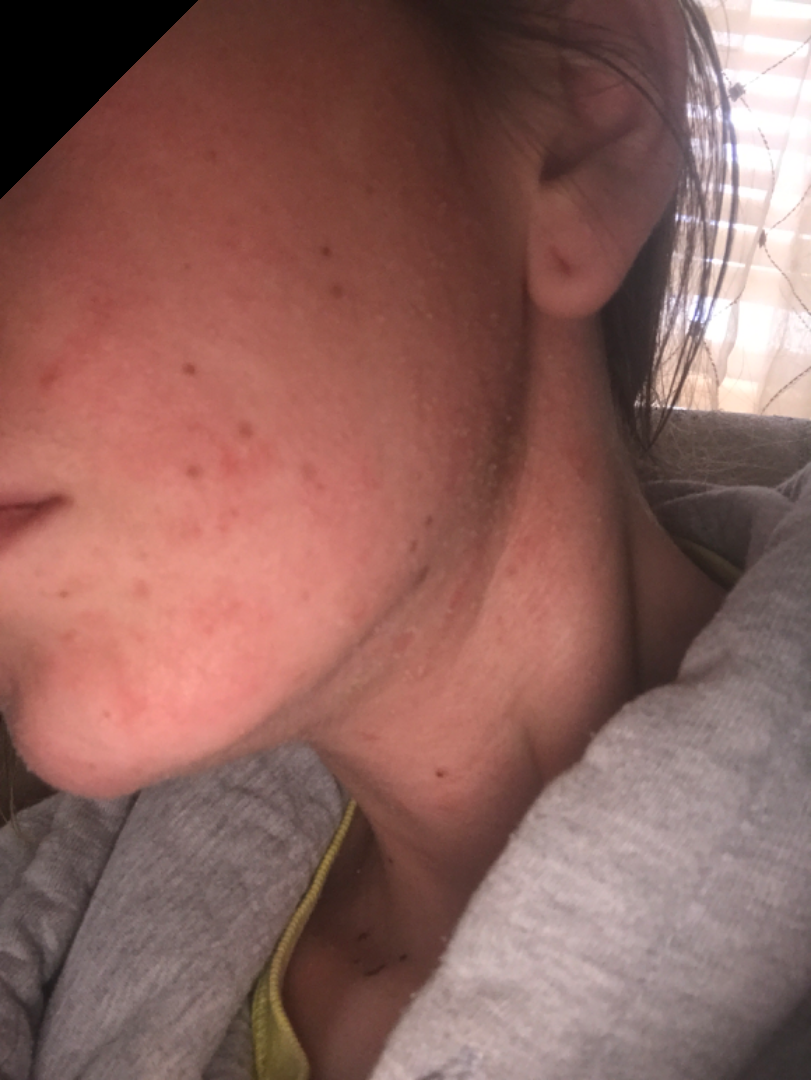The image was not sufficient for the reviewer to characterize the skin condition.